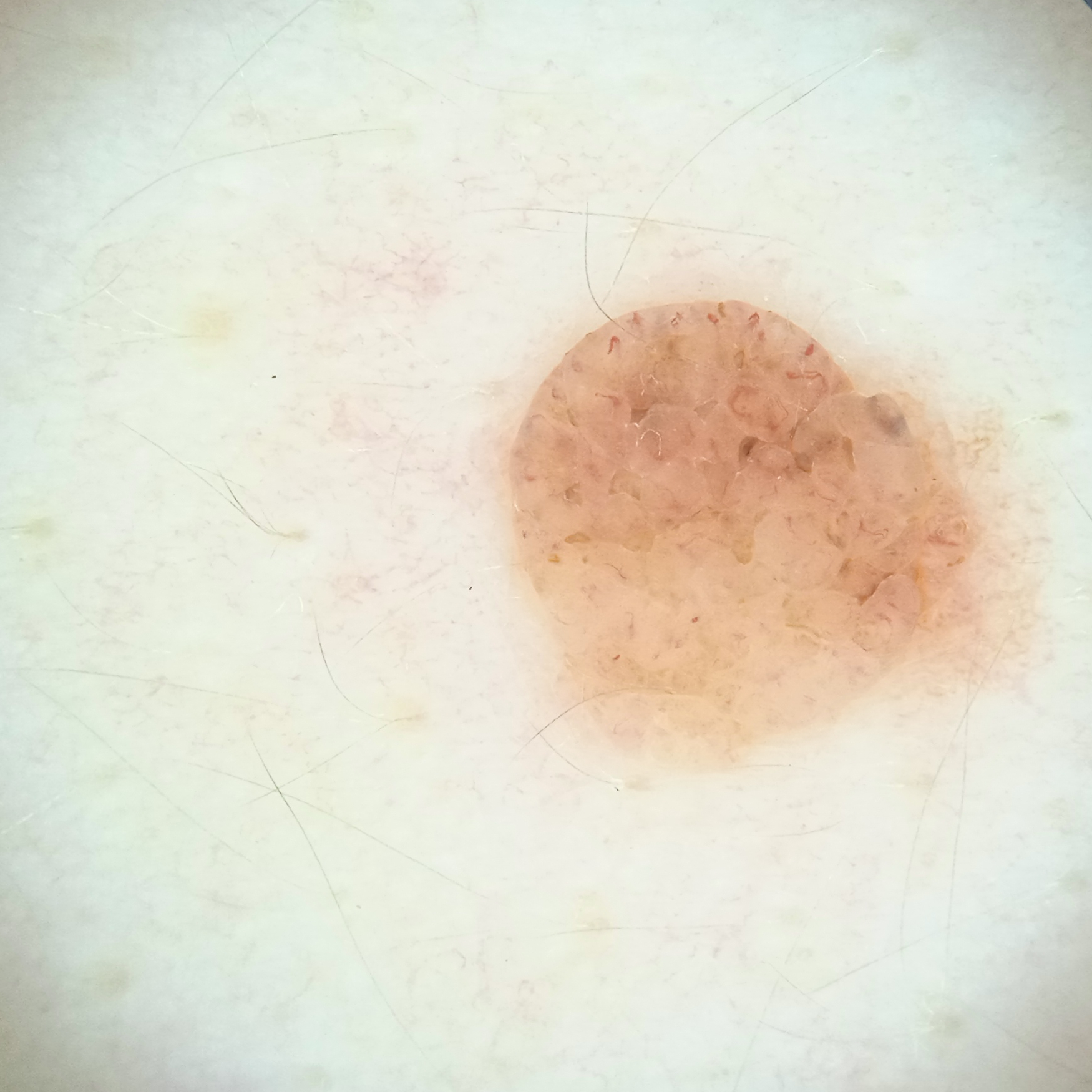sun_reaction: skin reddens with sun exposure
patient:
  age: 26
  sex: female
image: dermatoscopic image
lesion_location: the back
diagnosis:
  name: melanocytic nevus
  malignancy: benign